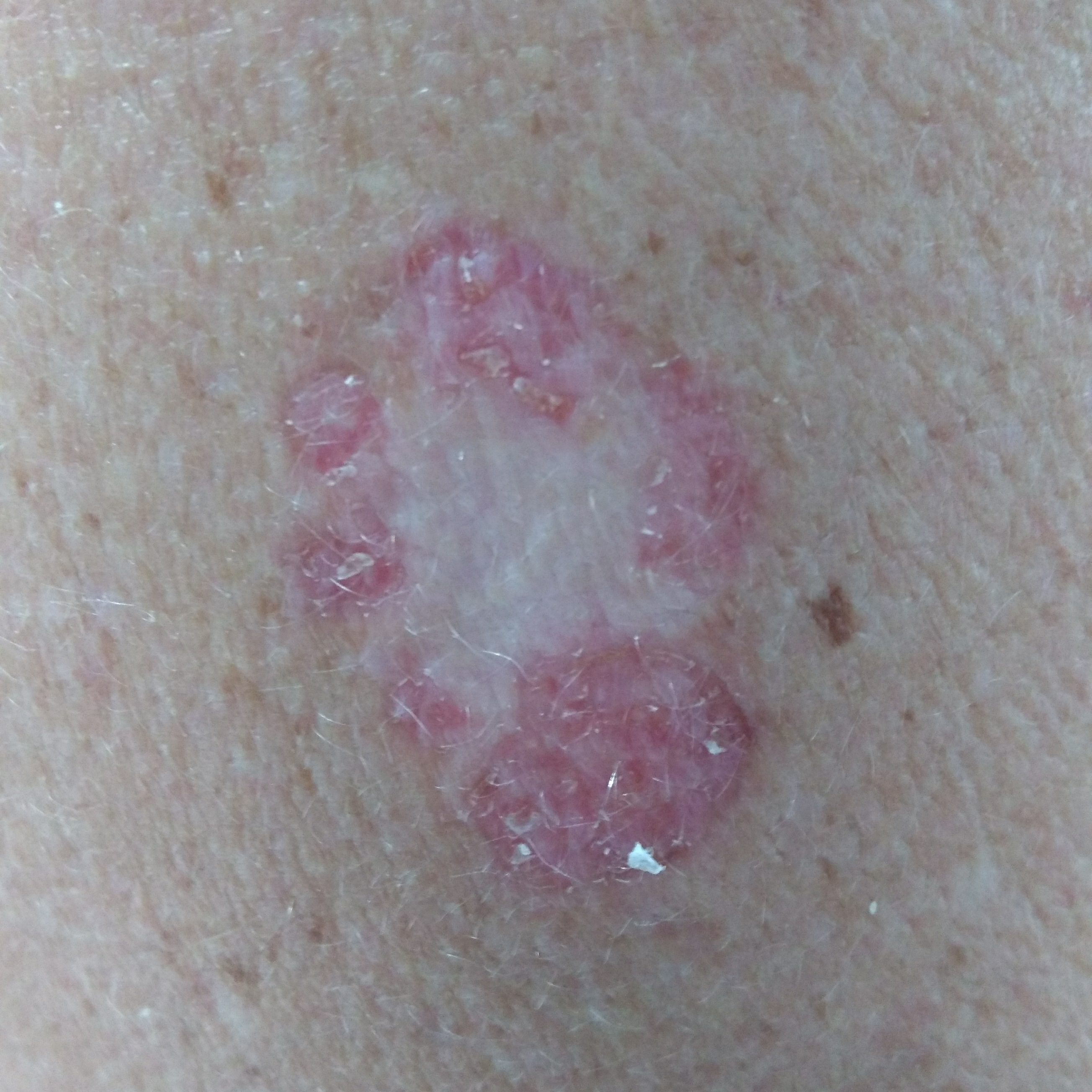| key | value |
|---|---|
| diagnostic label | basal cell carcinoma (biopsy-proven) |